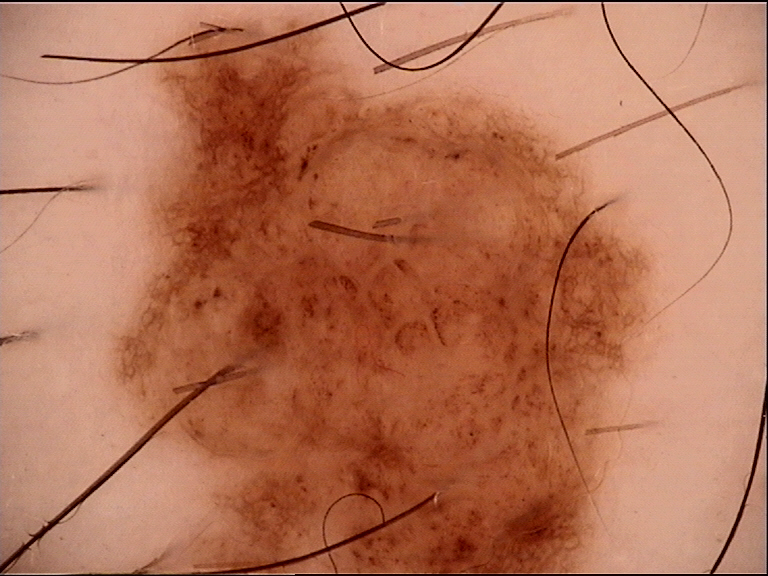image = dermoscopy
class = compound nevus (expert consensus)